The photograph is a close-up of the affected area; the back of the torso and arm are involved.
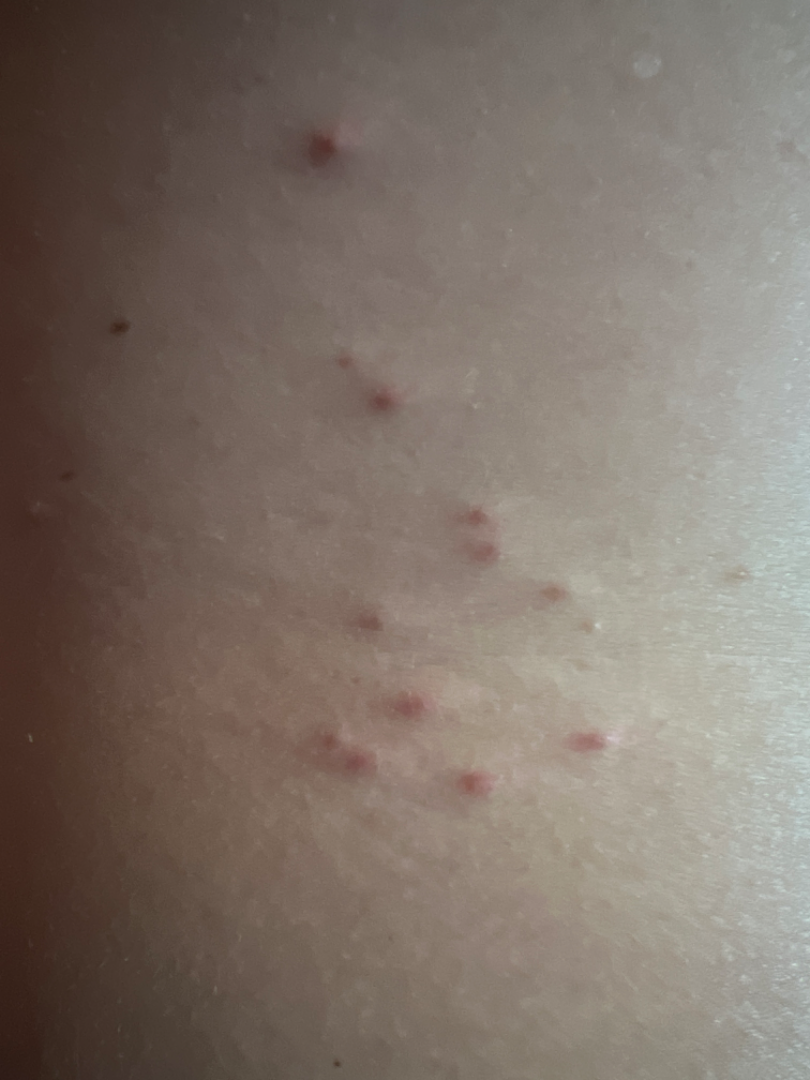No differential diagnosis could be assigned on photographic review.